A dermoscopy image of a single skin lesion · a female patient, in their mid- to late 80s or older.
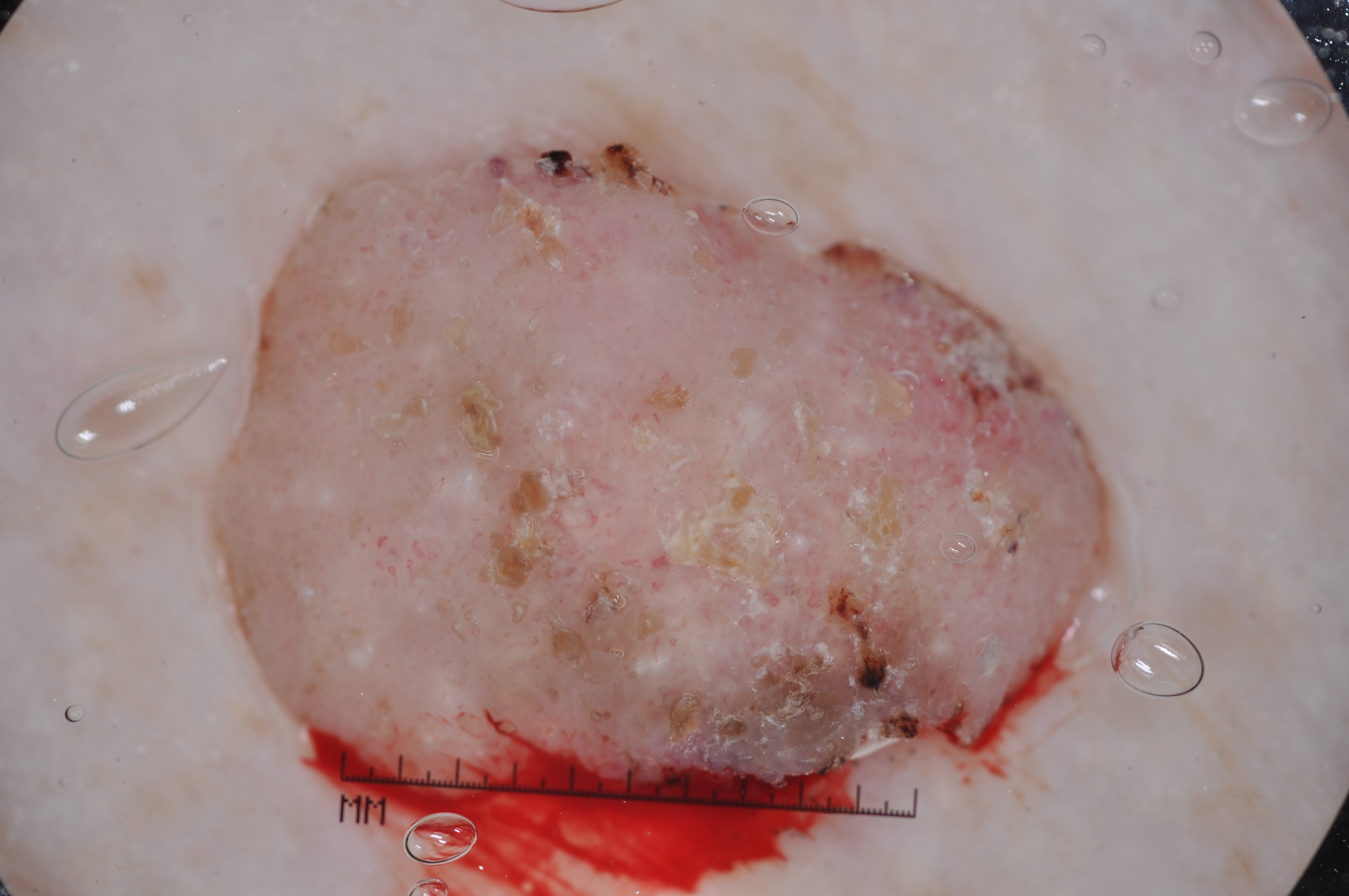| key | value |
|---|---|
| dermoscopic findings | milia-like cysts; absent: streaks, negative network, and pigment network |
| lesion margin | reaches the image border |
| lesion location | box(158, 105, 1138, 895) |
| assessment | a seborrheic keratosis |